The subject is male, the lesion involves the leg, the photo was captured at an angle — 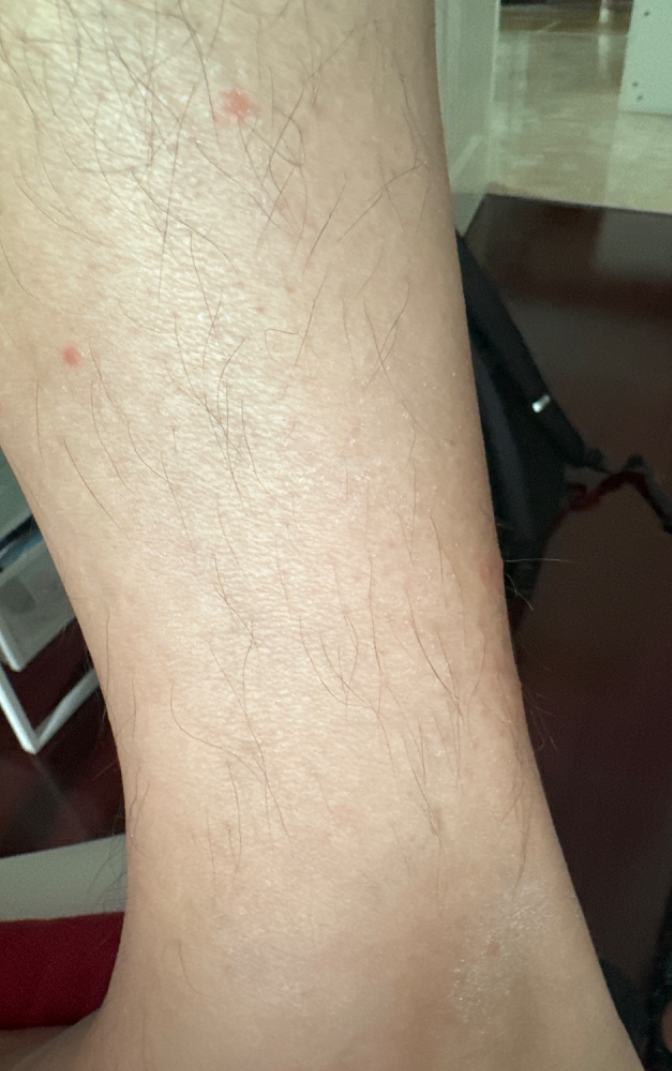Q: What conditions are considered?
A: in keeping with Insect Bite